The photograph was taken at an angle: 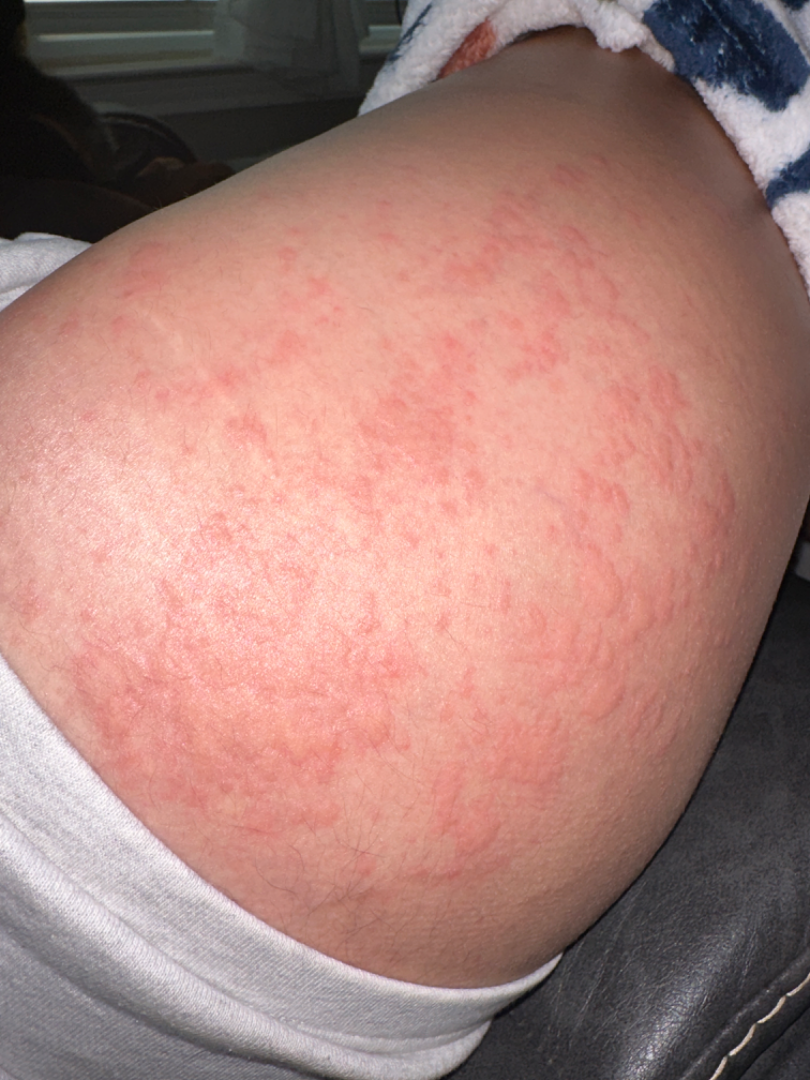On dermatologist assessment of the image, the impression is Urticaria.